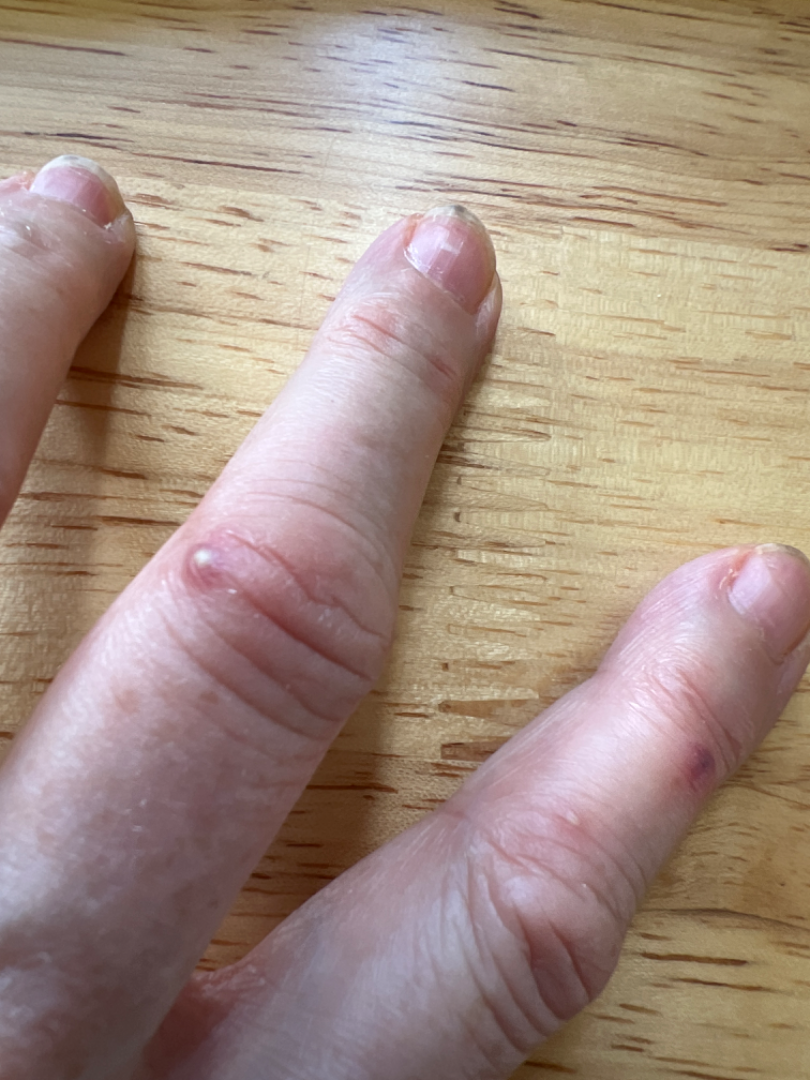{
  "shot_type": "close-up",
  "patient": "female",
  "patient_category": "a rash",
  "texture": "fluid-filled",
  "duration": "about one day",
  "body_site": "back of the hand",
  "symptoms": [
    "enlargement",
    "itching"
  ],
  "differential": {
    "tied_lead": [
      "Impetigo",
      "Chilblain",
      "Leukocytoclastic Vasculitis"
    ]
  }
}